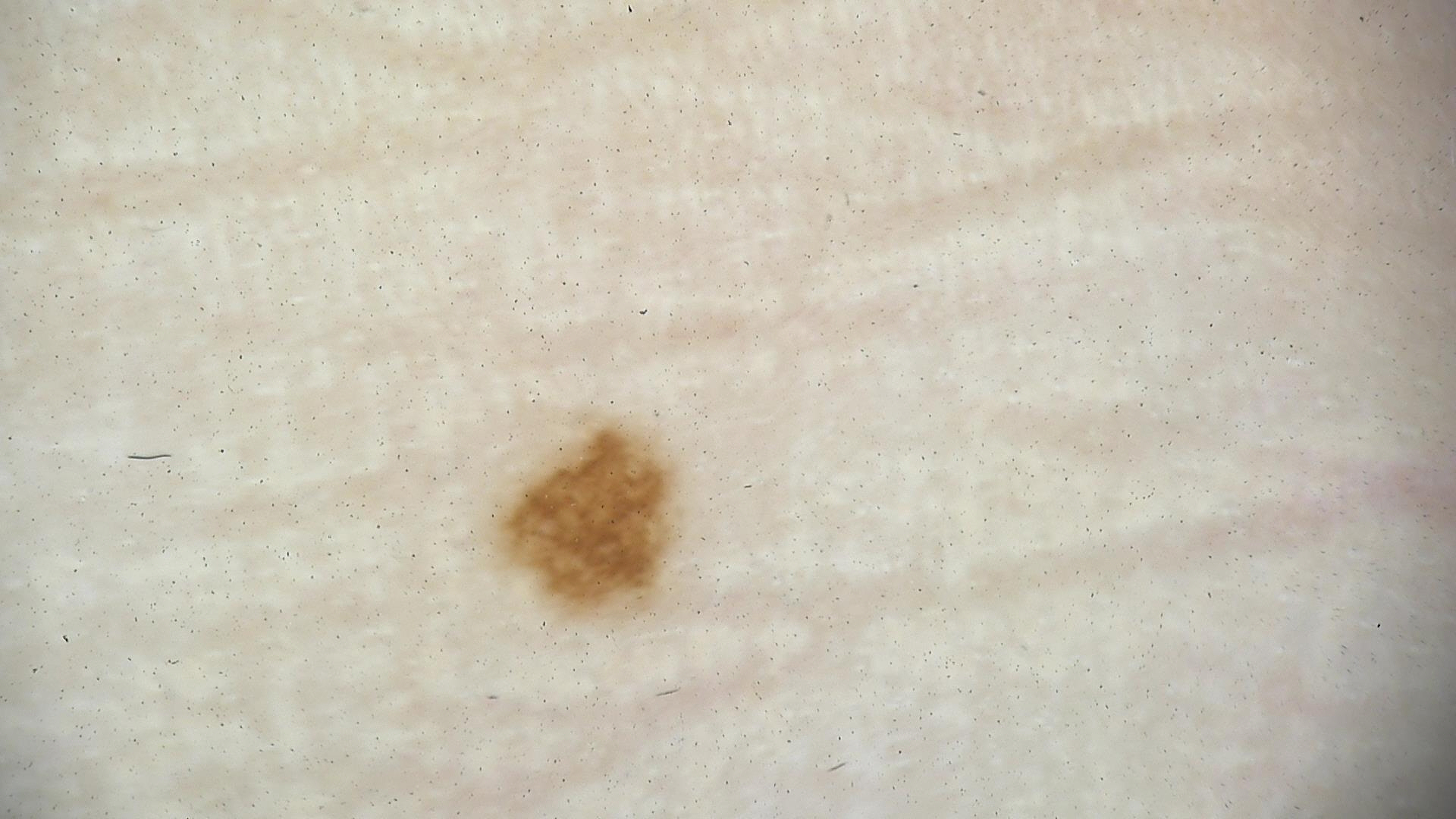Findings:
A dermoscopic photograph of a skin lesion.
Impression:
The diagnostic label was a benign lesion — an acral dysplastic junctional nevus.